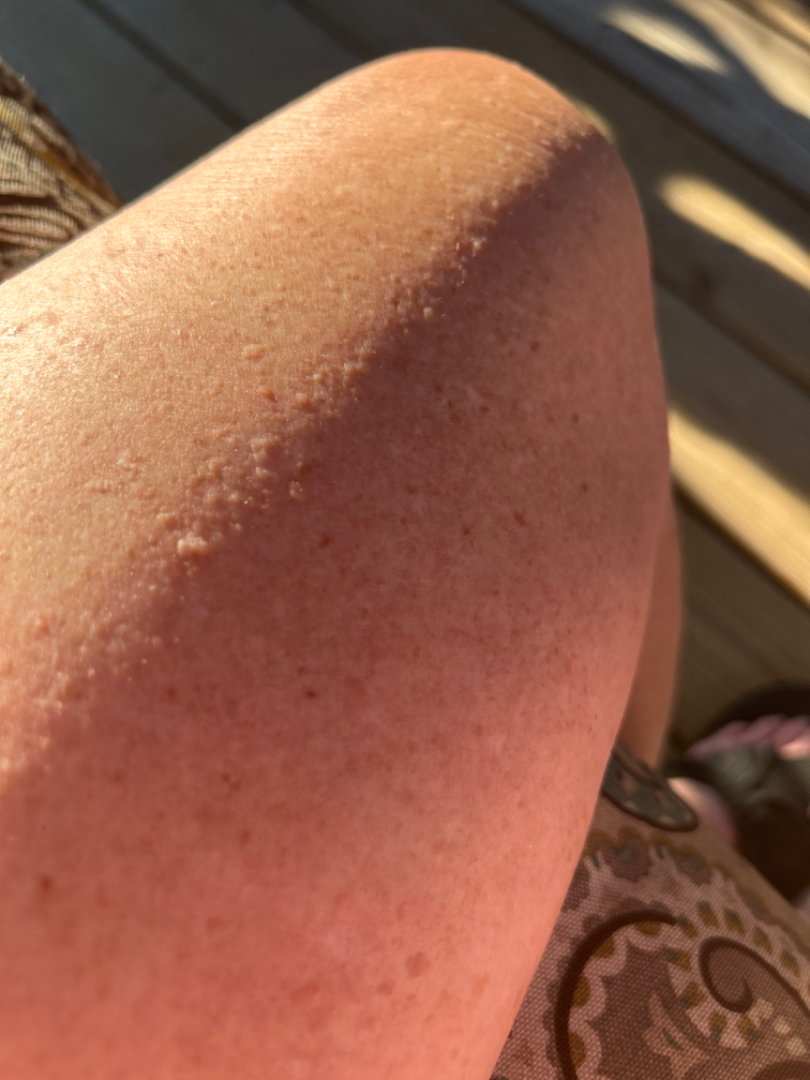Q: What was the assessment?
A: not assessable
Q: What is the framing?
A: close-up